The patient says their skin tans without first burning · collected as part of a research study, without a referral diagnosis · a dermoscopic image of a skin lesion · the patient describes having a moderate number of moles · a female patient aged 47 · on a questionnaire the patient reported a history of sunbed use — 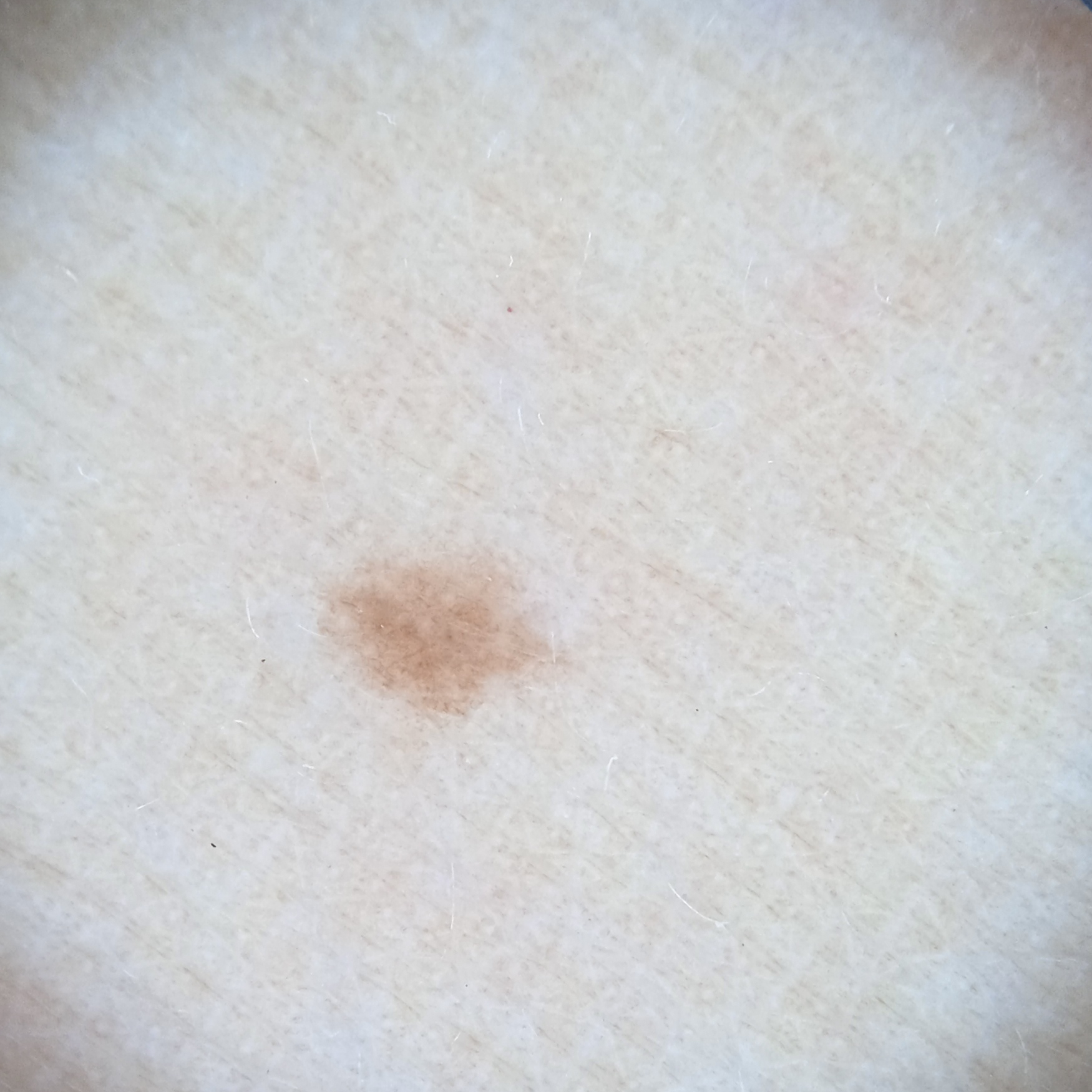Findings:
Located on an arm. Measuring roughly 2.7 mm.
Impression:
Dermatologist review favored a melanocytic nevus.